A dermoscopic photograph of a skin lesion.
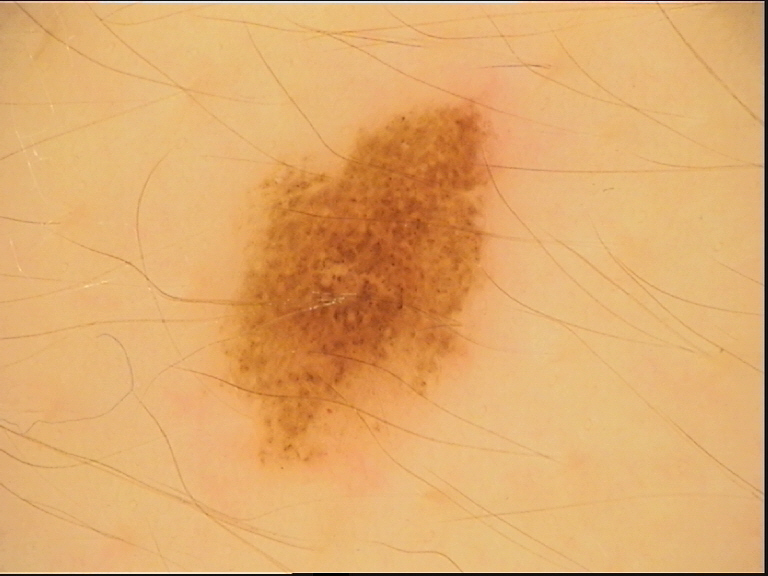The diagnosis was a dysplastic compound nevus.